Skin tone: Fitzpatrick phototype II; human graders estimated MST 3 · an image taken at a distance — 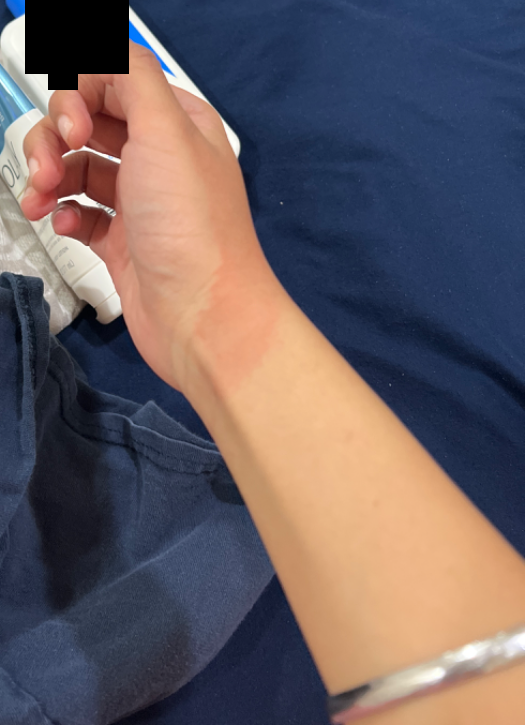On remote dermatologist review, Photodermatitis (favored); Burn erythema of back of hand (possible).